This is a close-up image; female patient, age 50–59; located on the head or neck — 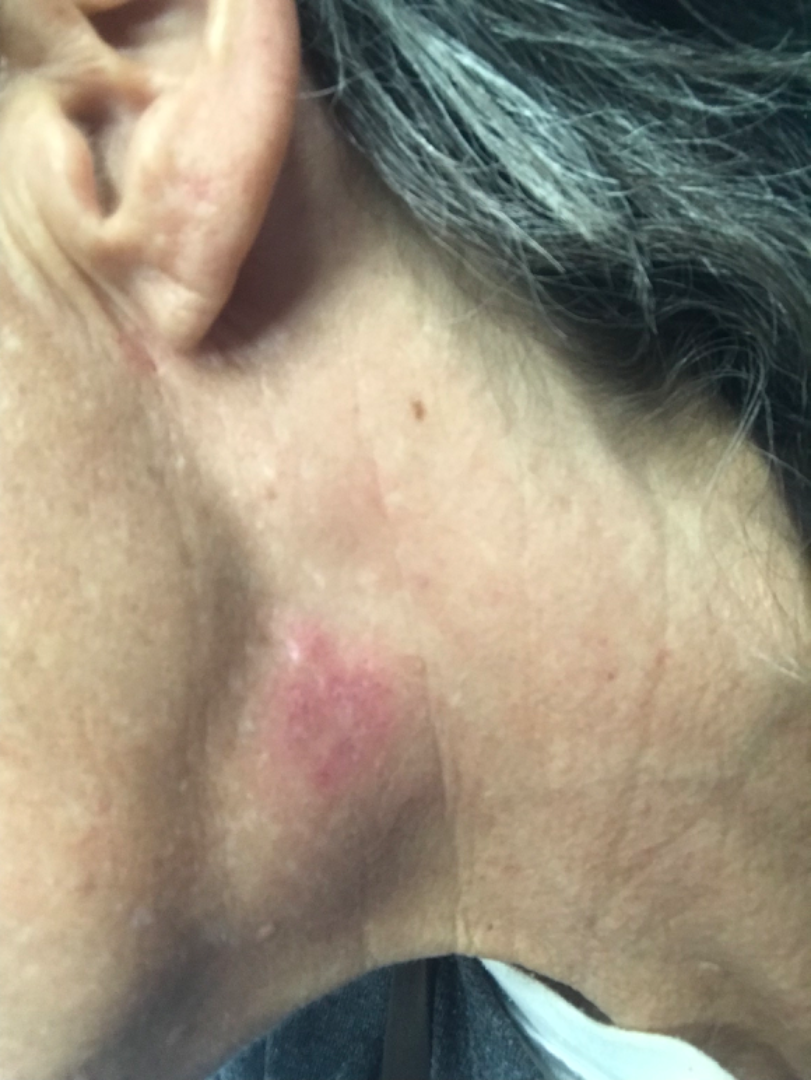Findings:
– assessment: not assessable